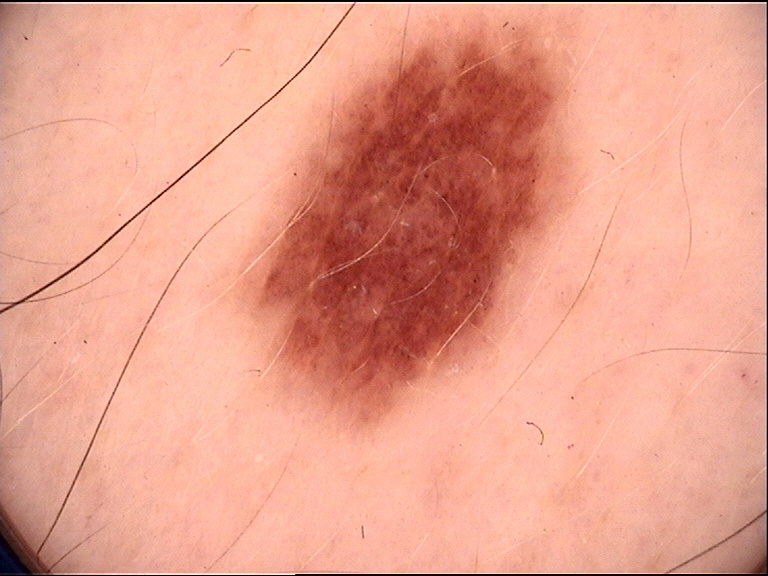label: dysplastic junctional nevus (expert consensus).